Skin tone: Fitzpatrick phototype I · the lesion is described as raised or bumpy · male subject, age 60–69 · reported lesion symptoms include itching · close-up view · the lesion involves the arm, back of the torso, leg and head or neck.
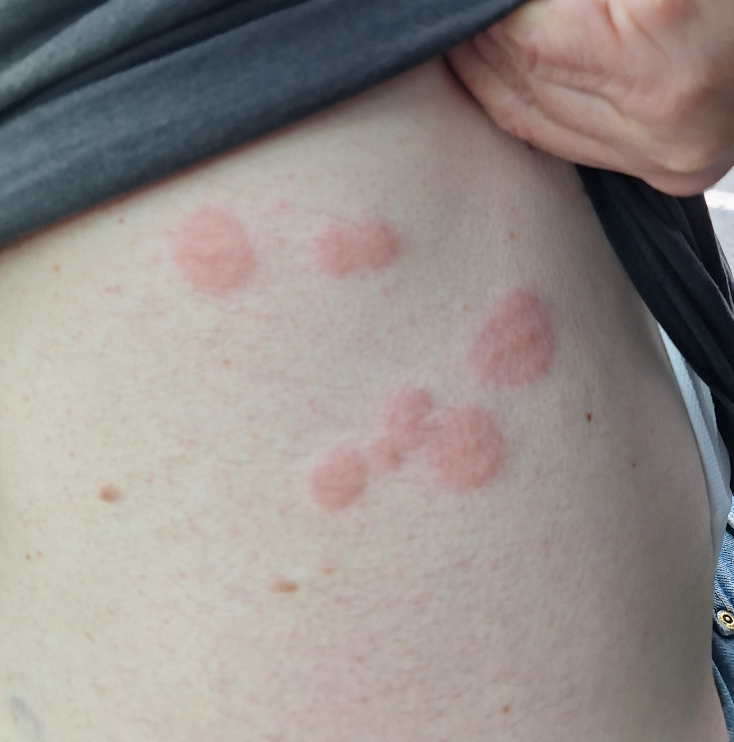Case summary:
- differential: Insect Bite (100%)